A skin lesion imaged with a dermatoscope: 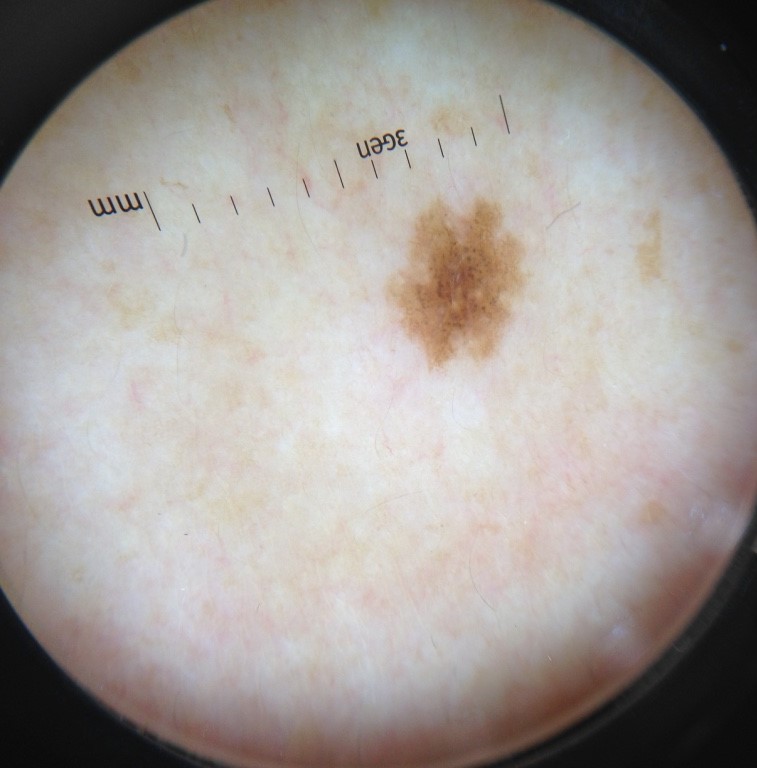– assessment · dysplastic junctional nevus (expert consensus)